A female patient 67 years old. A dermatoscopic image of a skin lesion. Acquired for a research image collection, with no referral diagnosis:
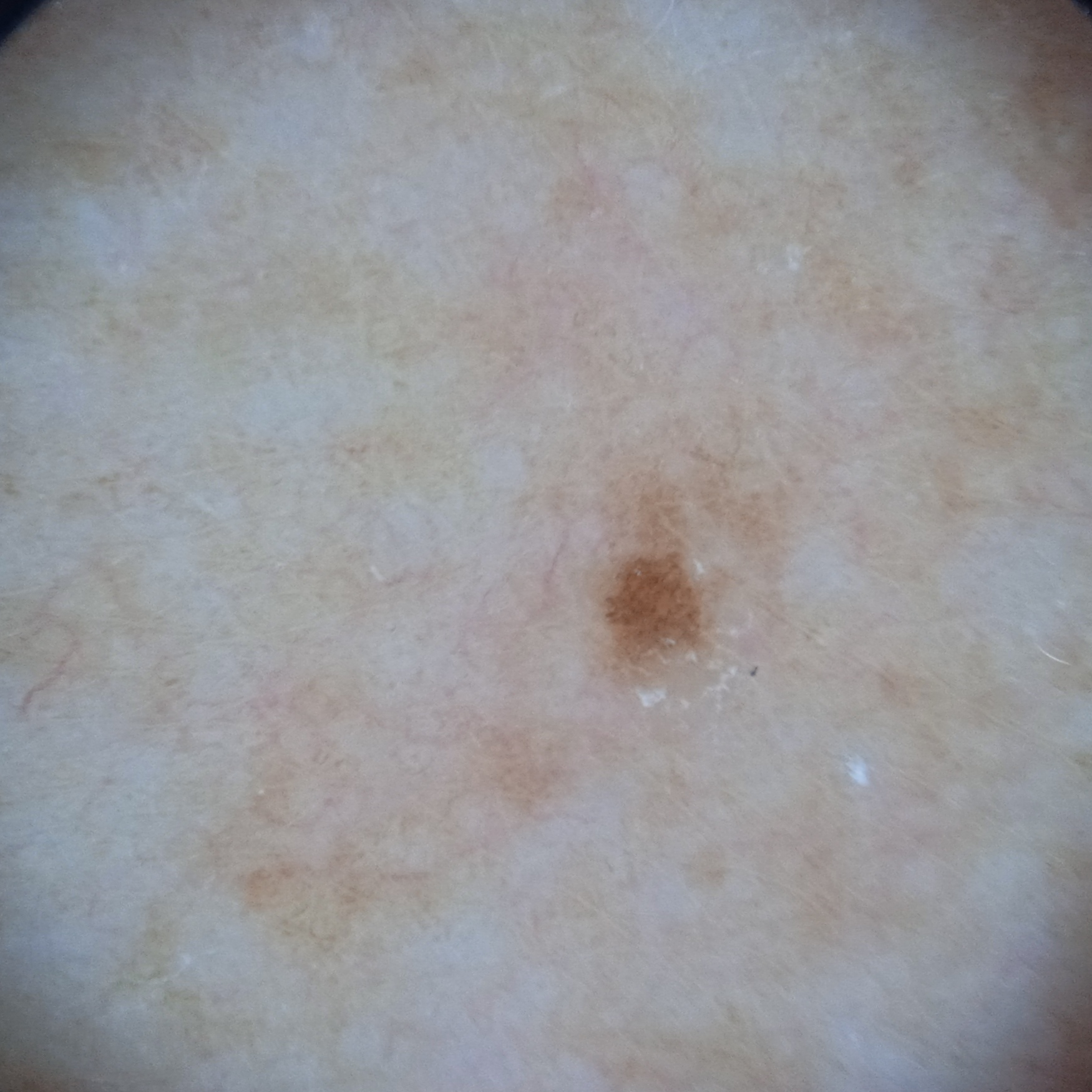| field | value |
|---|---|
| assessment | melanocytic nevus (dermatologist consensus) |